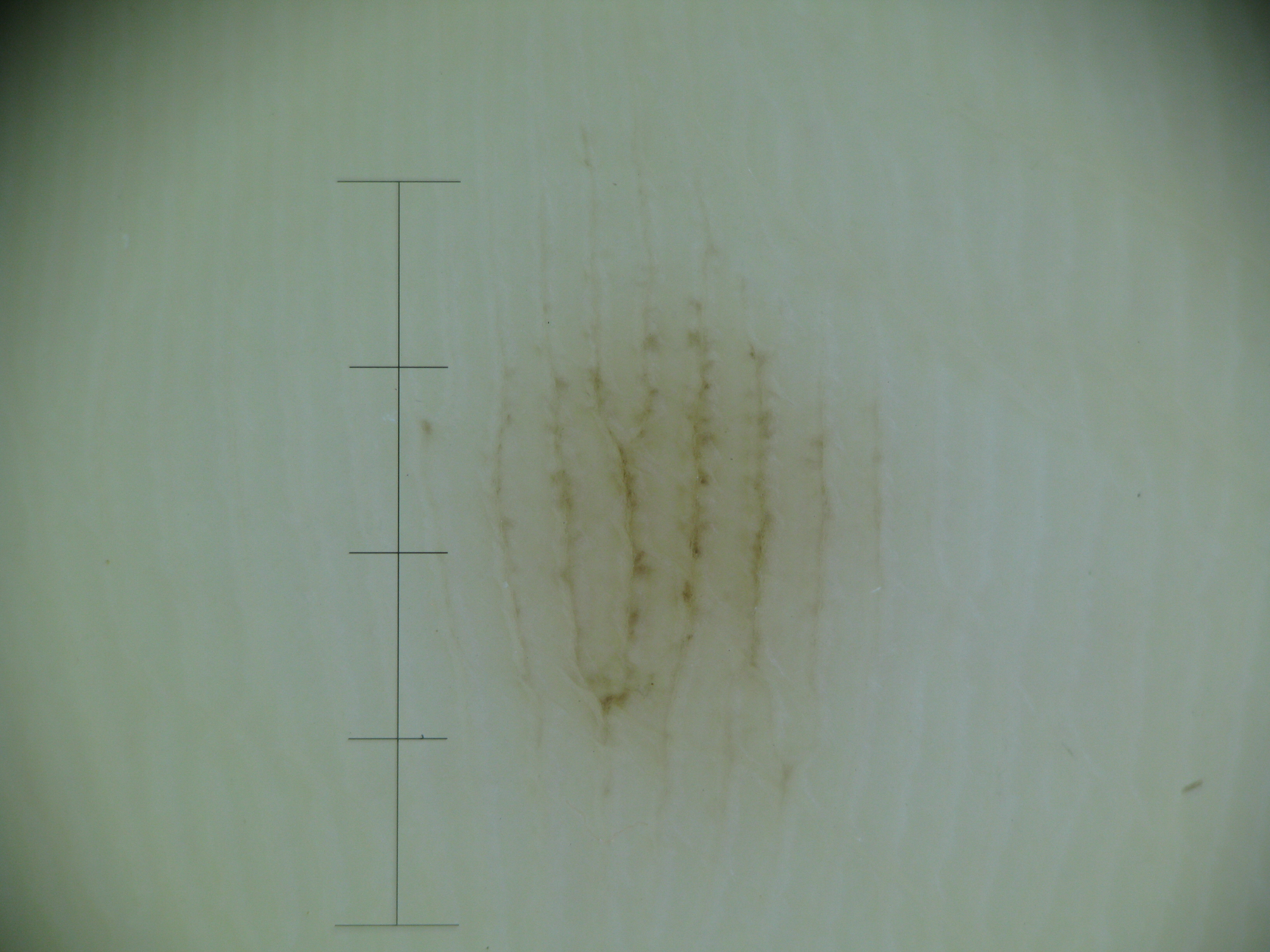Conclusion: Diagnosed as an acral junctional nevus.